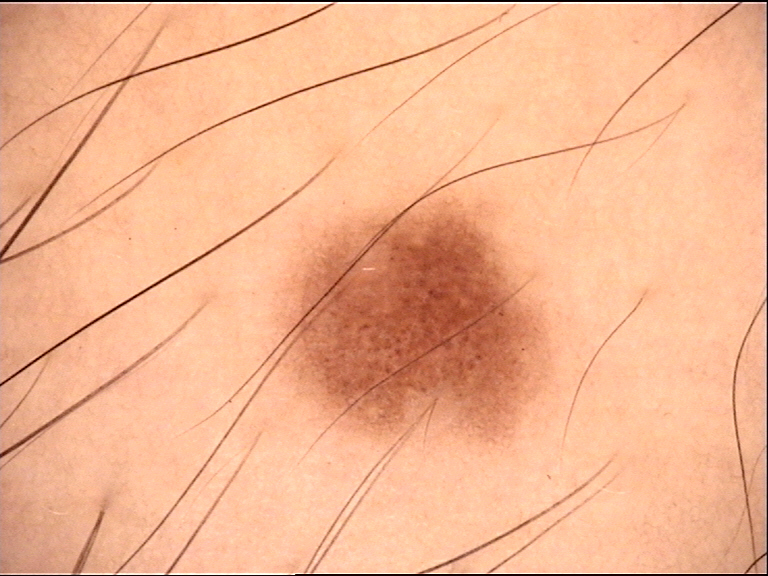Diagnosed as a junctional nevus.